The patient is a male aged approximately 35 · dermoscopy of a skin lesion: 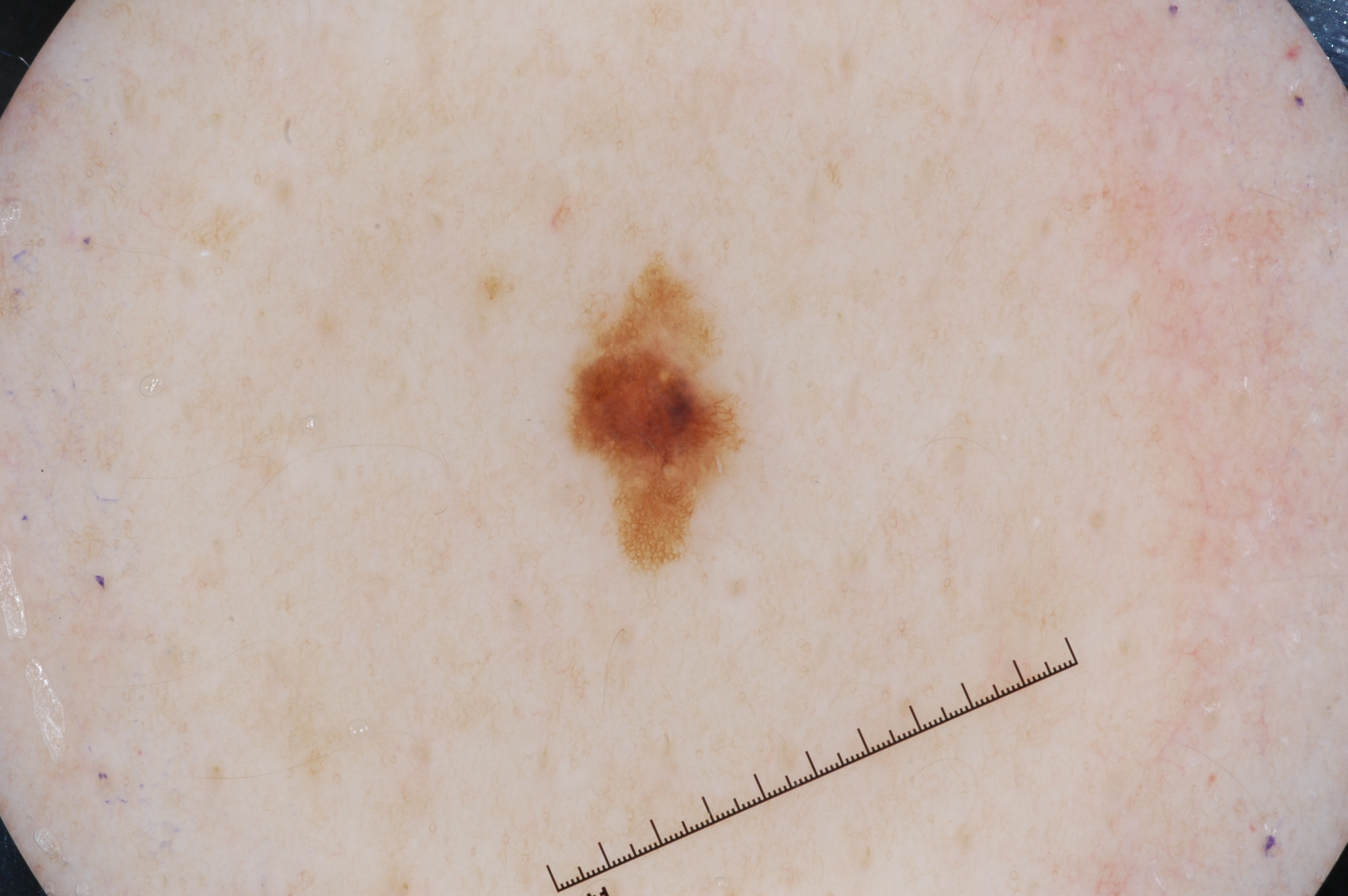As (left, top, right, bottom), the lesion spans bbox=[569, 280, 737, 546]. The lesion occupies roughly 3% of the field. Dermoscopic review identifies pigment network; no negative network, milia-like cysts, or streaks. Clinically diagnosed as a melanocytic nevus.